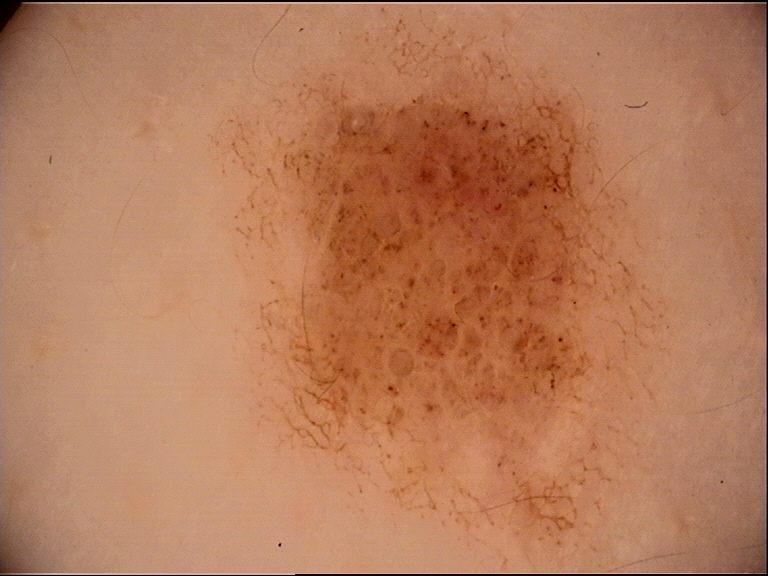Findings:
* class: compound nevus (expert consensus)